A female patient in their mid-80s or older. A dermatoscopic image of a skin lesion — 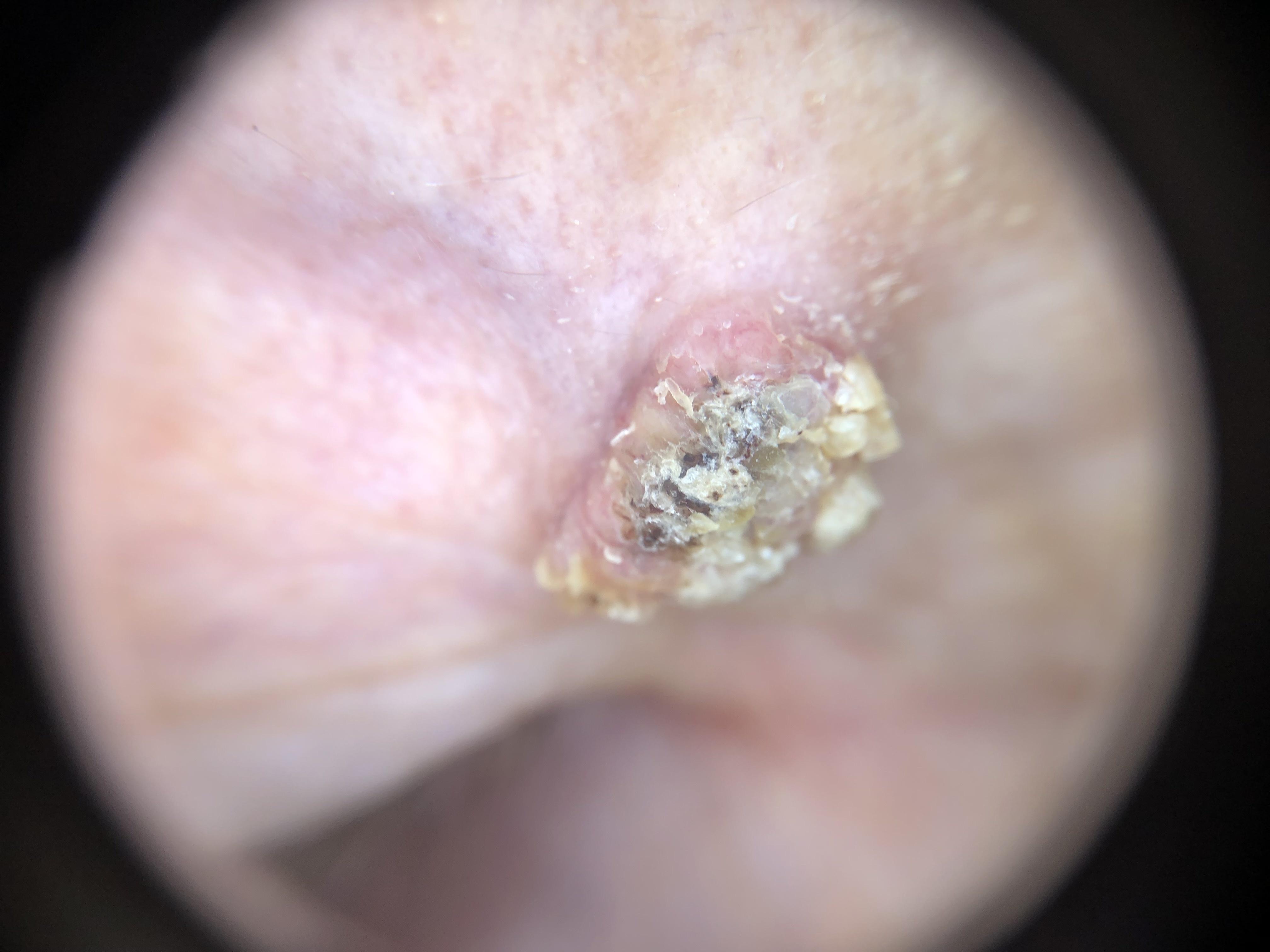Q: What is the anatomic site?
A: the head or neck
Q: What did the workup show?
A: Squamous cell carcinoma (biopsy-proven)